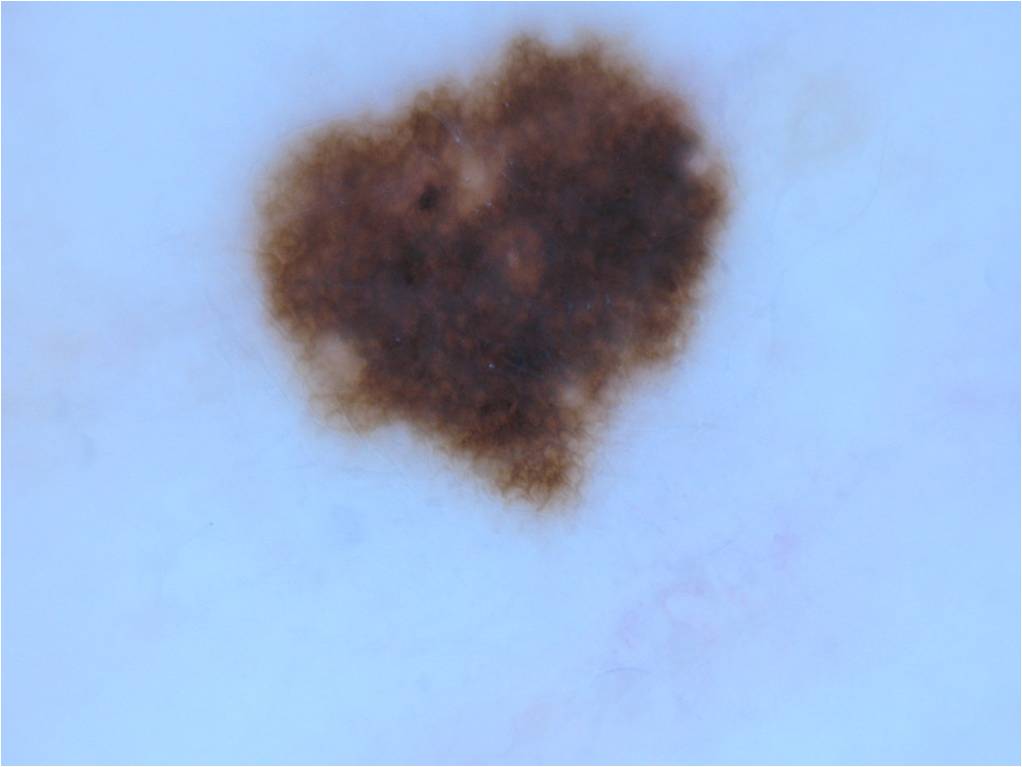Case summary:
– patient · female, aged around 55
– image type · dermoscopy
– dermoscopic pattern · pigment network and globules; absent: streaks, negative network, and milia-like cysts
– location · <box>248, 28, 734, 511</box>
– extent · ~21% of the field
– diagnostic label · a melanocytic nevus